Female patient, age 30–39. This image was taken at a distance — 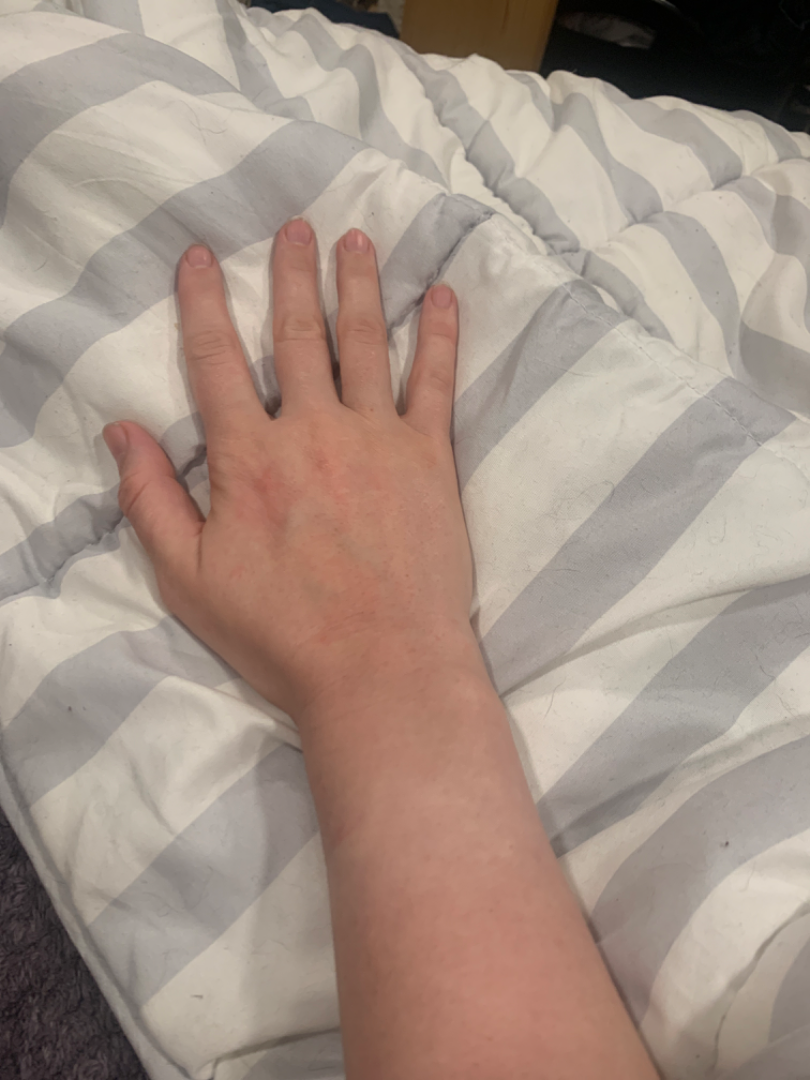Assessment: Photodermatitis, Allergic Contact Dermatitis and Irritant Contact Dermatitis were each considered, in no particular order.